A dermatoscopic image of a skin lesion:
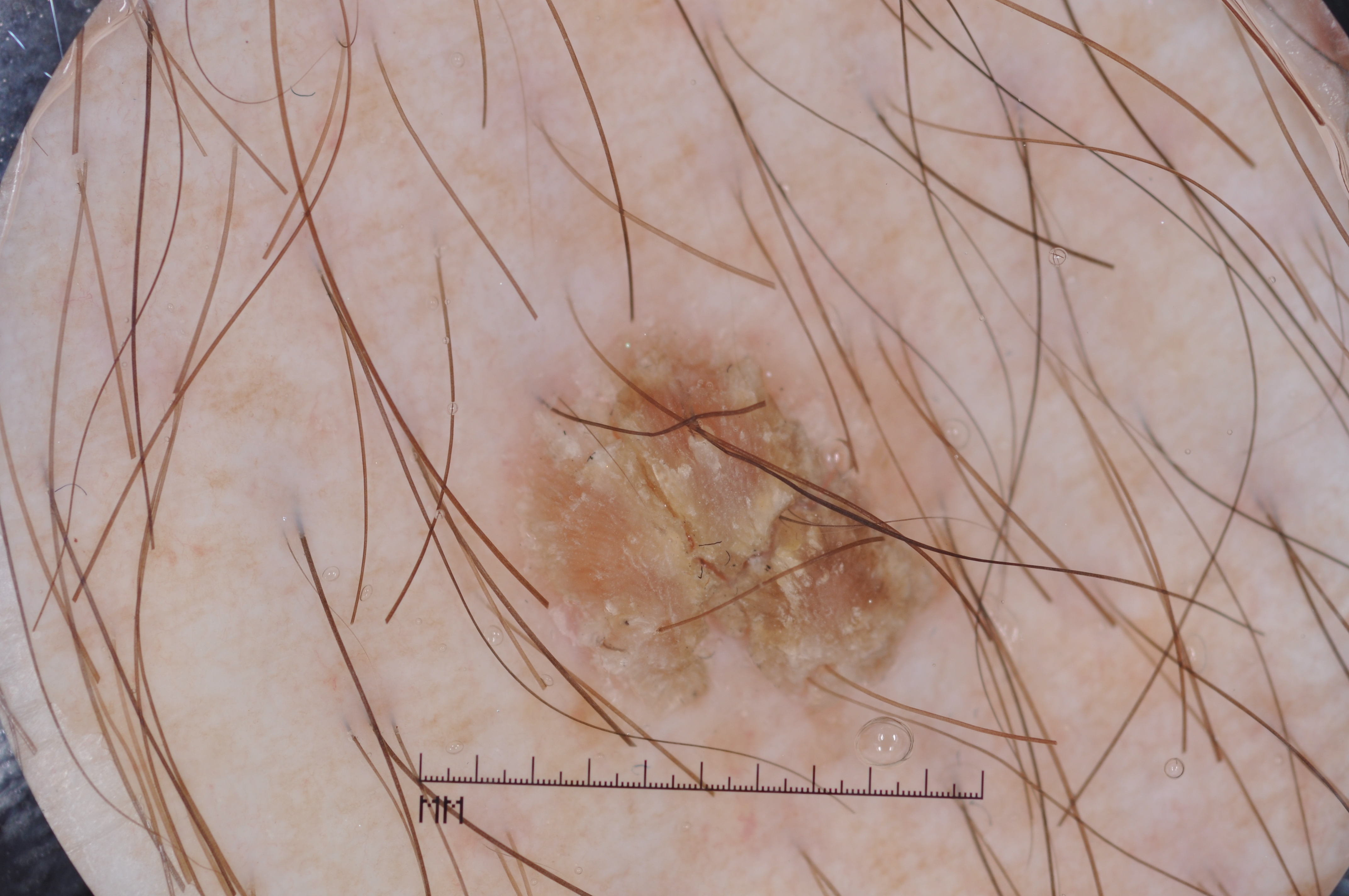Dermoscopically, the lesion shows no pigment network, milia-like cysts, streaks, or negative network. With coordinates (x1, y1, x2, y2), the visible lesion spans 482, 287, 983, 805. Diagnosed as a seborrheic keratosis, a benign skin lesion.